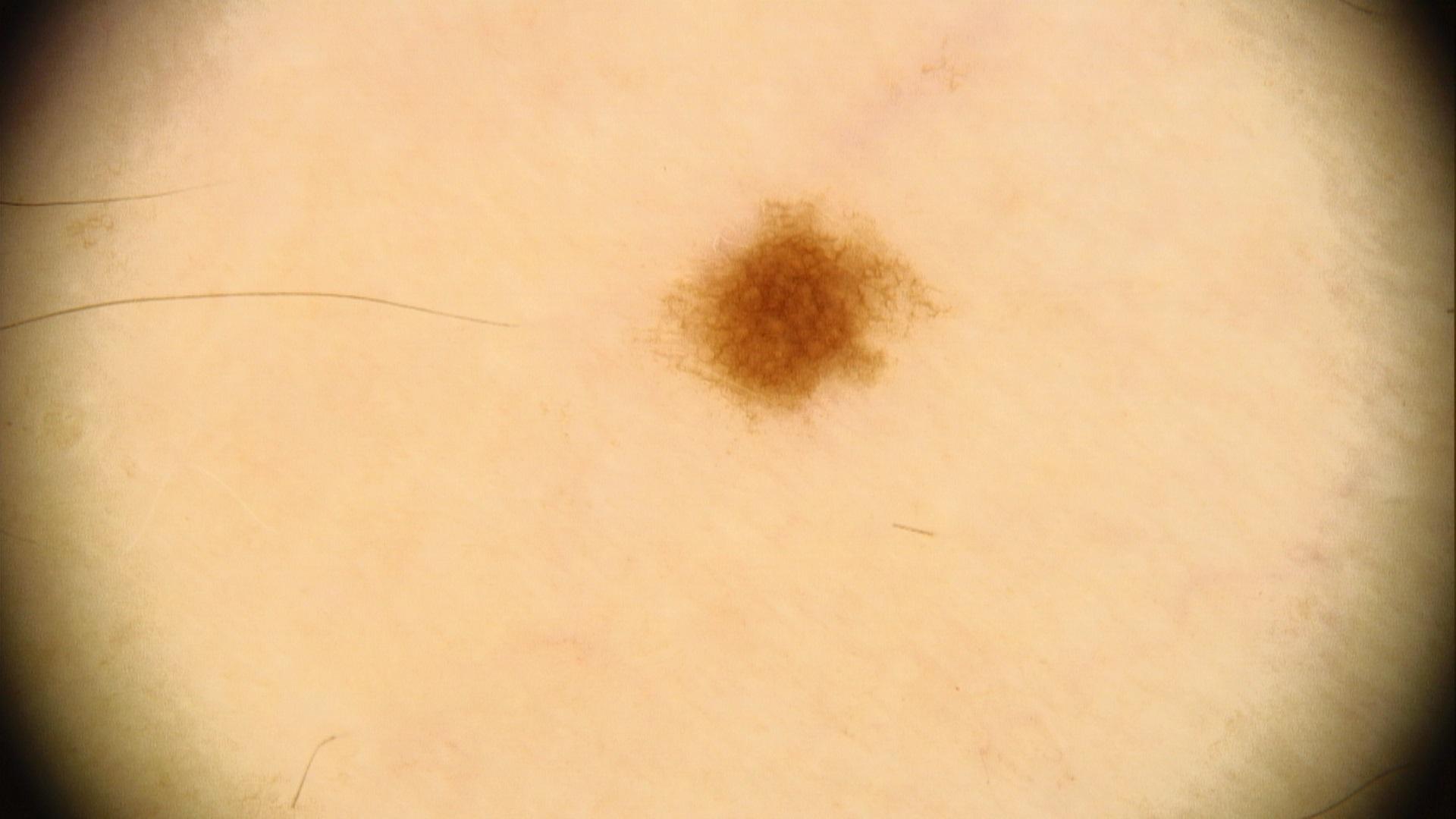A female subject about 55 years old. Fitzpatrick IV. A dermoscopic photograph of a skin lesion. The lesion is located on a lower extremity. The diagnostic impression was a benign lesion — a nevus.